The photo was captured at a distance.
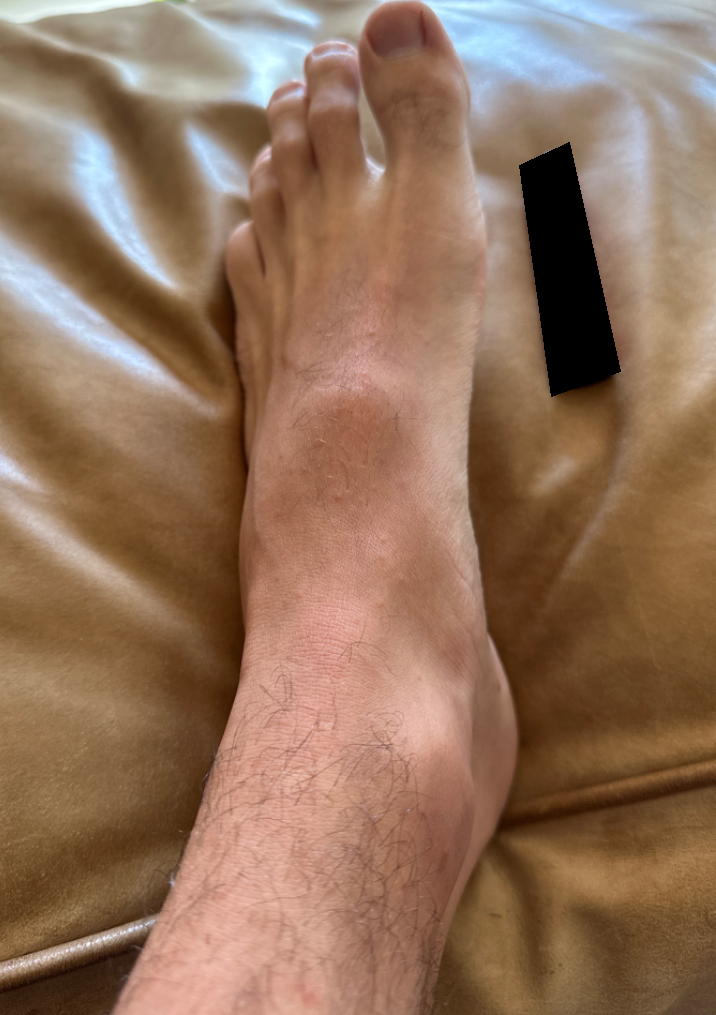Findings:
* assessment — could not be assessed